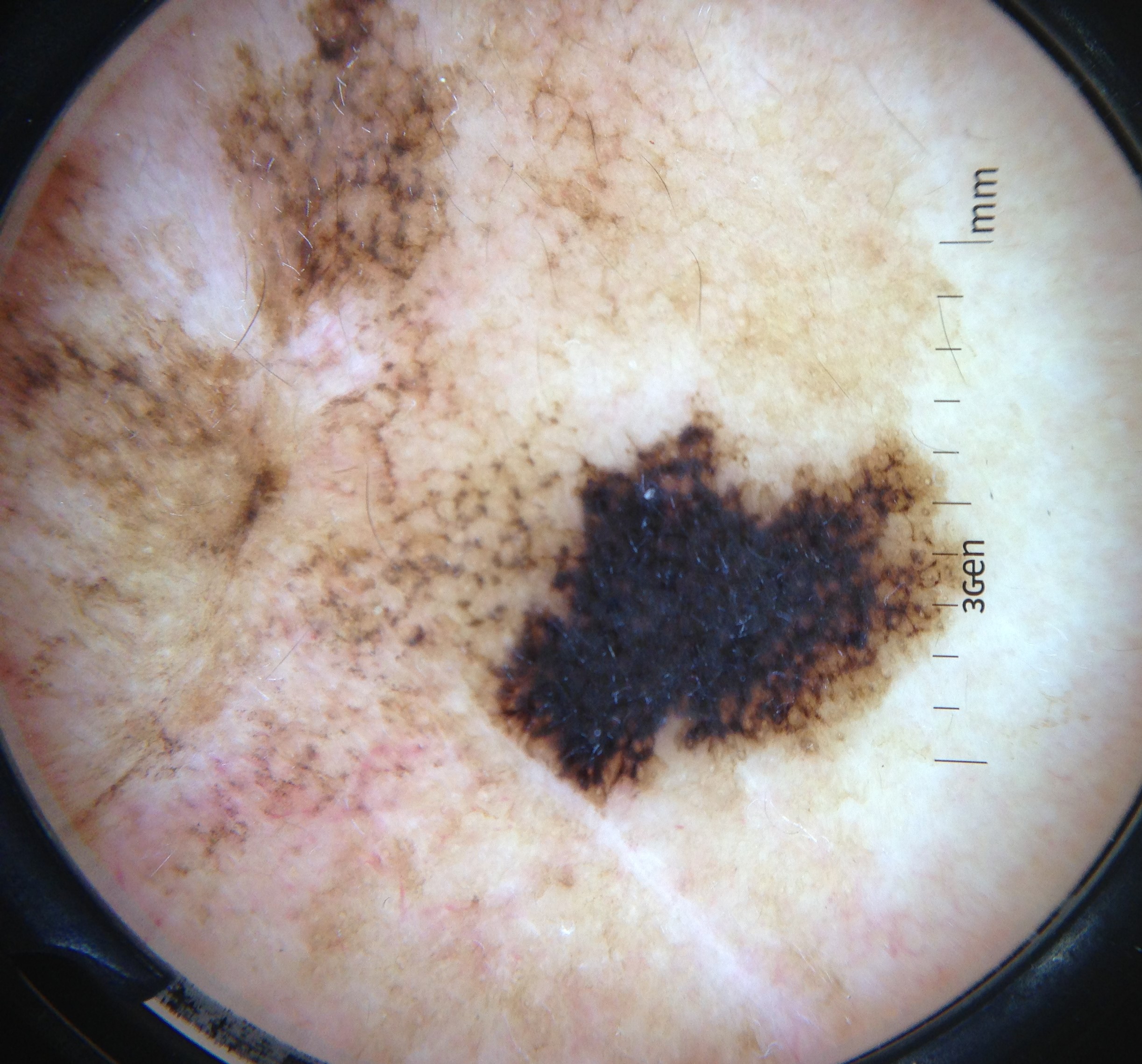Diagnosis: Histopathology confirmed a lentigo maligna.